History notes pesticide exposure and prior malignancy (patient or family). Skin type IV. A clinical photograph of a skin lesion. A male patient in their mid-60s:
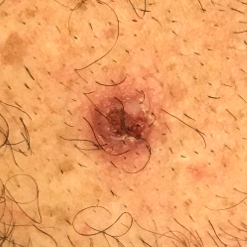Located on the chest. The lesion measures approximately 1 × 1 mm. The patient reports that the lesion has grown, is elevated, and itches, but has not bled and does not hurt. On biopsy, the diagnosis was a basal cell carcinoma.